A female subject aged 60 · a dermoscopy image of a skin lesion · the referring clinician suspected basal cell carcinoma · the patient describes having few moles overall.
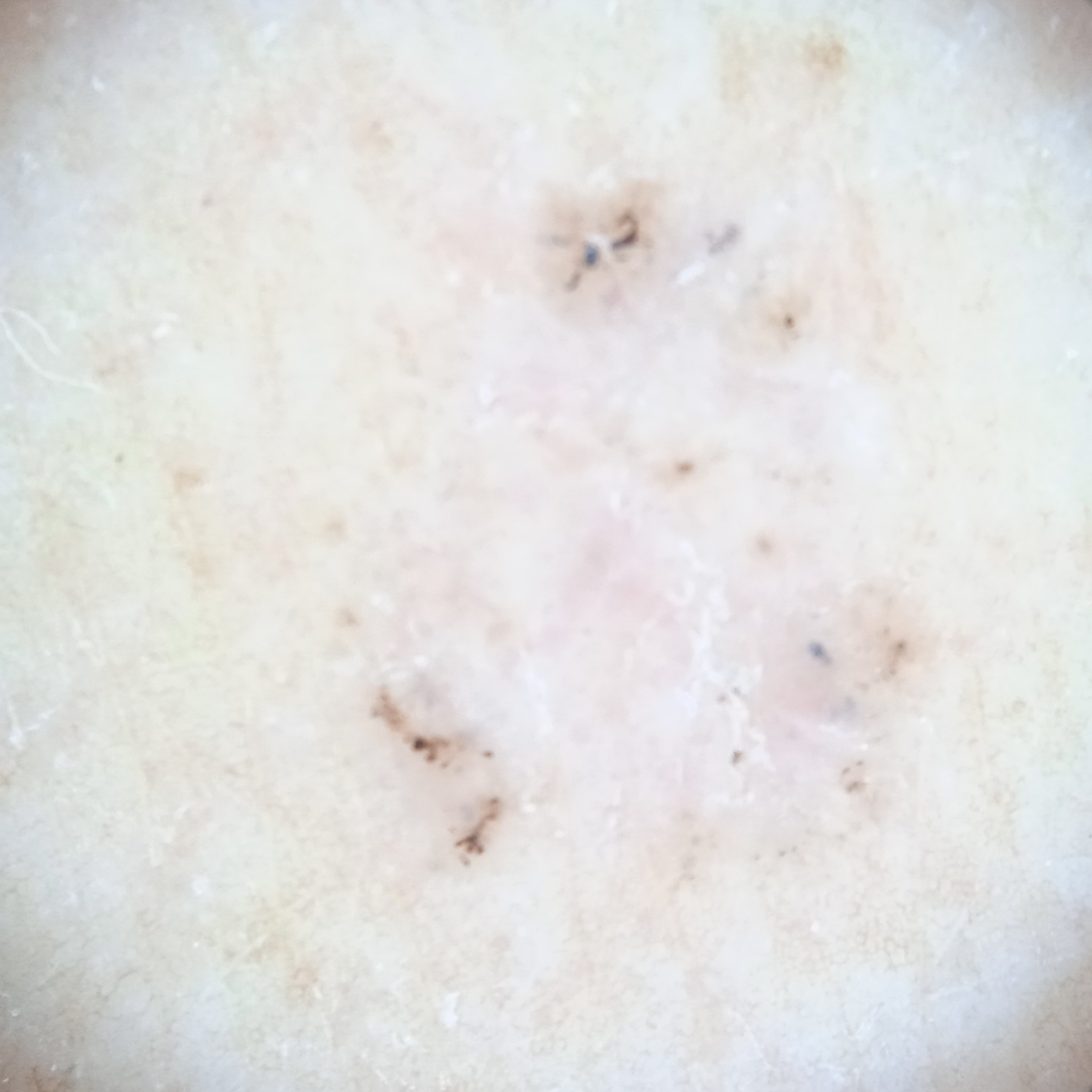Located on the back.
The lesion is about 7.8 mm across.
The consensus diagnosis for this lesion was a basal cell carcinoma.